Located on the arm; the patient reported no systemic symptoms; the lesion is described as raised or bumpy; self-categorized by the patient as a rash; the subject is 50–59, female; this image was taken at a distance; the lesion is associated with itching: 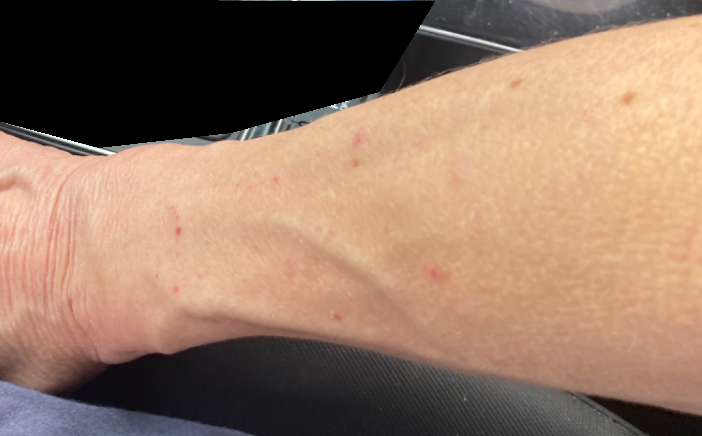assessment: could not be assessed